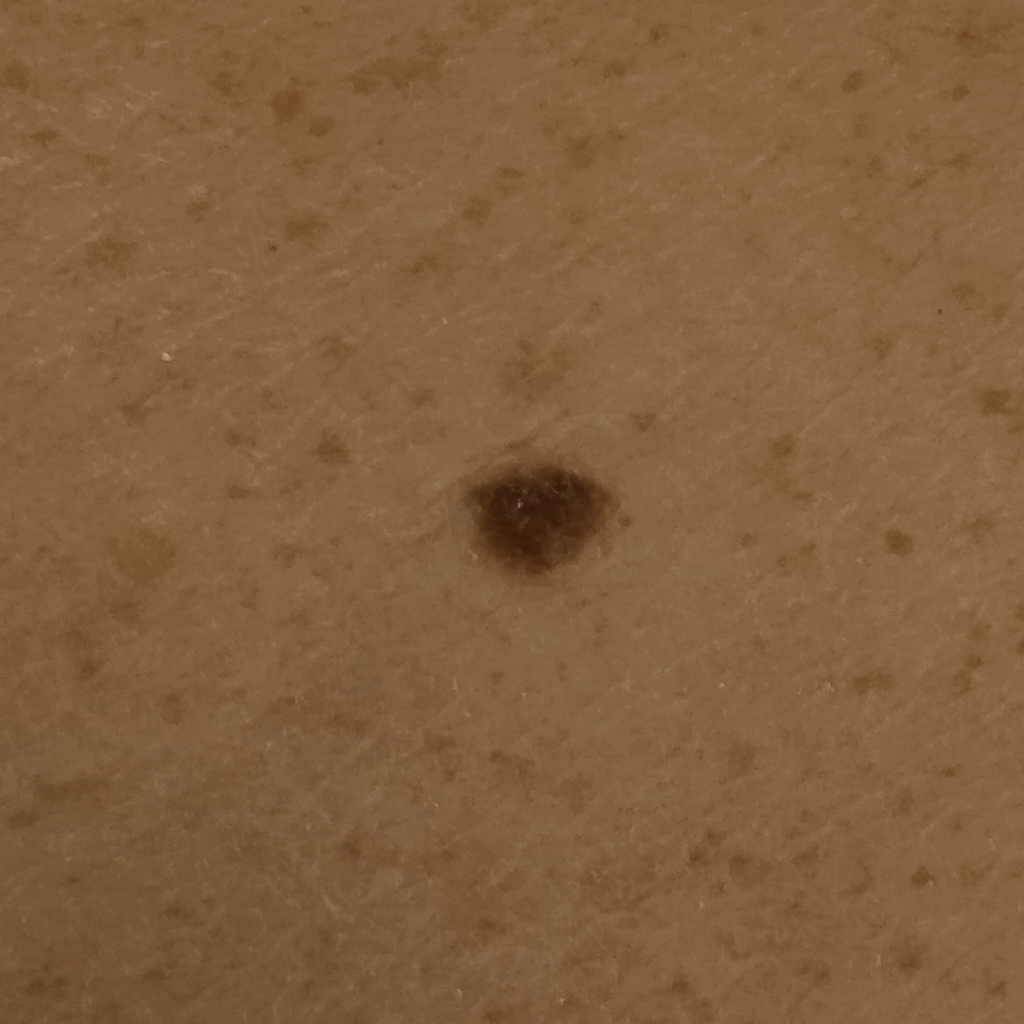subject: male, 72 years of age; referral context: research study (no referral diagnosis); nevus count: few melanocytic nevi overall; sun reaction: skin reddens with sun exposure; risk factors: a personal history of cancer; modality: clinical photograph; site: the back; diameter: 5.6 mm; diagnostic label: melanocytic nevus (dermatologist consensus).